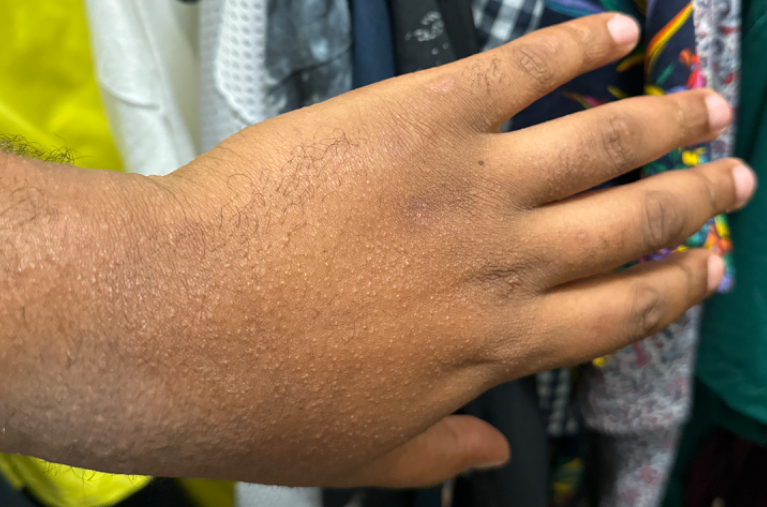The subject is 30–39, male. Symptoms reported: bothersome appearance, itching and enlargement. This image was taken at a distance. Present for one to four weeks. The lesion involves the arm and back of the hand. The lesion is described as raised or bumpy. Keratosis pilaris (weight 0.67); Miliaria (weight 0.33).